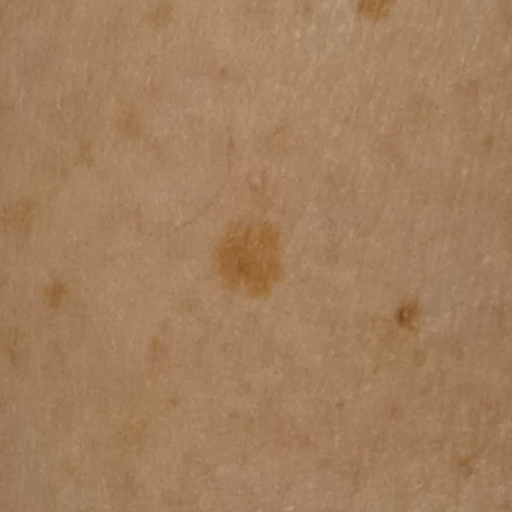| field | value |
|---|---|
| referral context | research study (no referral diagnosis) |
| relevant history | a personal history of cancer, a personal history of skin cancer |
| nevus count | few melanocytic nevi overall |
| sun reaction | skin reddens with sun exposure |
| patient | female, age 71 |
| site | an arm |
| size | 1.7 mm |
| assessment | melanocytic nevus (dermatologist consensus) |